This is a close-up image — 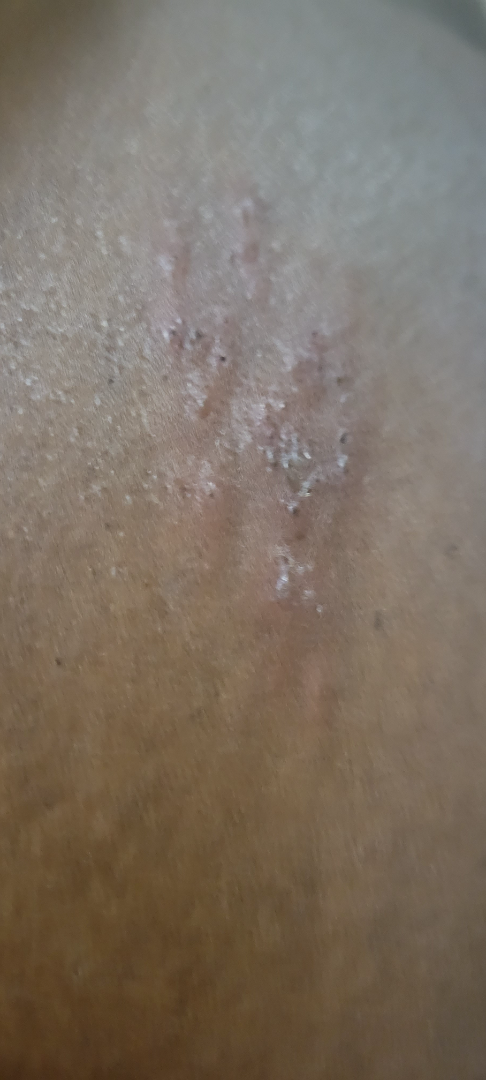Impression: The dermatologist could not determine a likely condition from the photograph alone. History: Skin tone: Fitzpatrick skin type V; lay reviewers estimated MST 4 or 7 (two reviewer pools disagreed). Texture is reported as raised or bumpy. Reported duration is less than one week. Self-categorized by the patient as a rash.